The patient reports no personal history of skin cancer. Imaged for a research study, with no referral diagnosis recorded. The patient says their skin reddens with sun exposure. Few moles overall by the patient's own estimate: 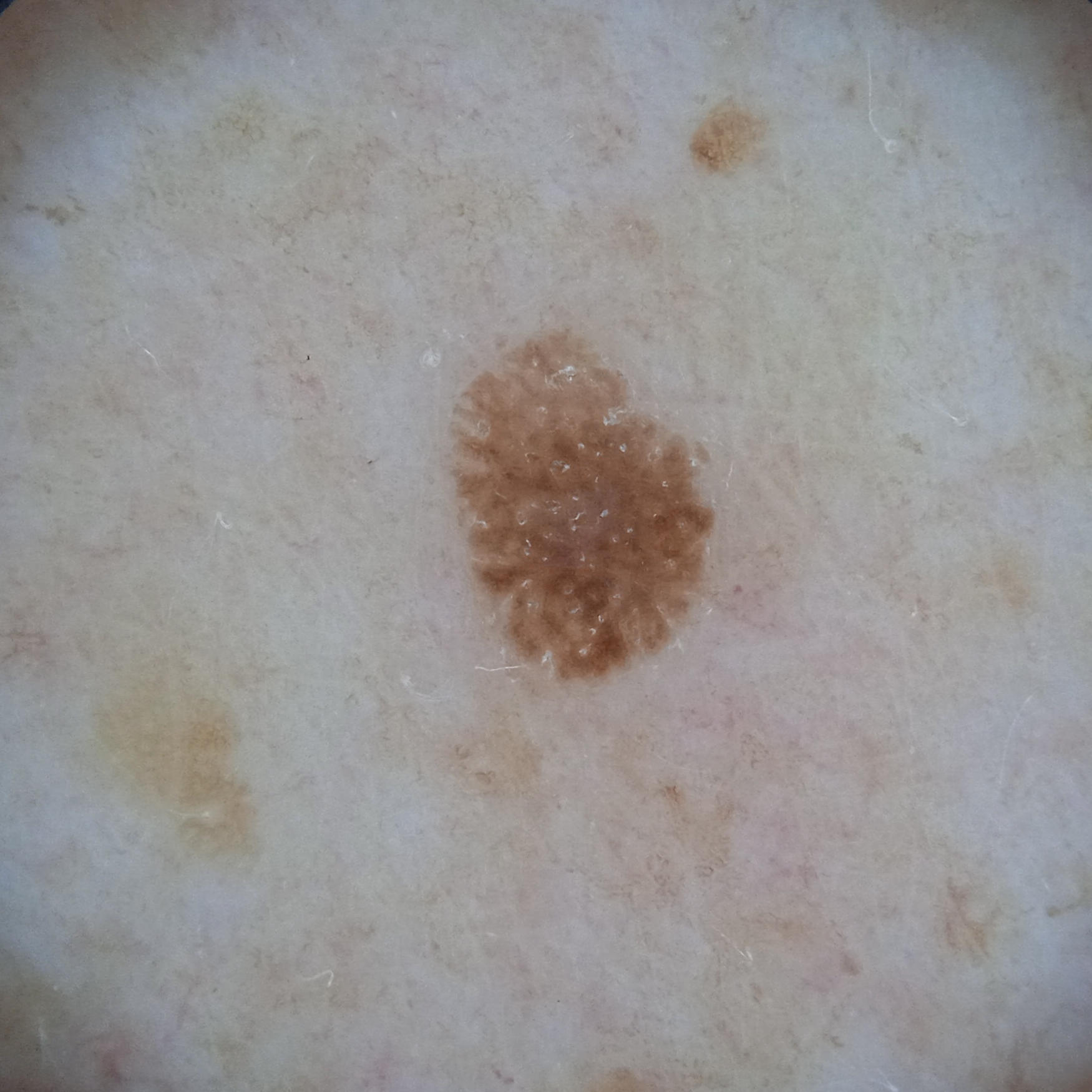The lesion is on the back. The lesion is about 4.3 mm across. On independent review by four dermatologists, the agreed diagnosis was a seborrheic keratosis; agreement among the reviewers was unanimous.